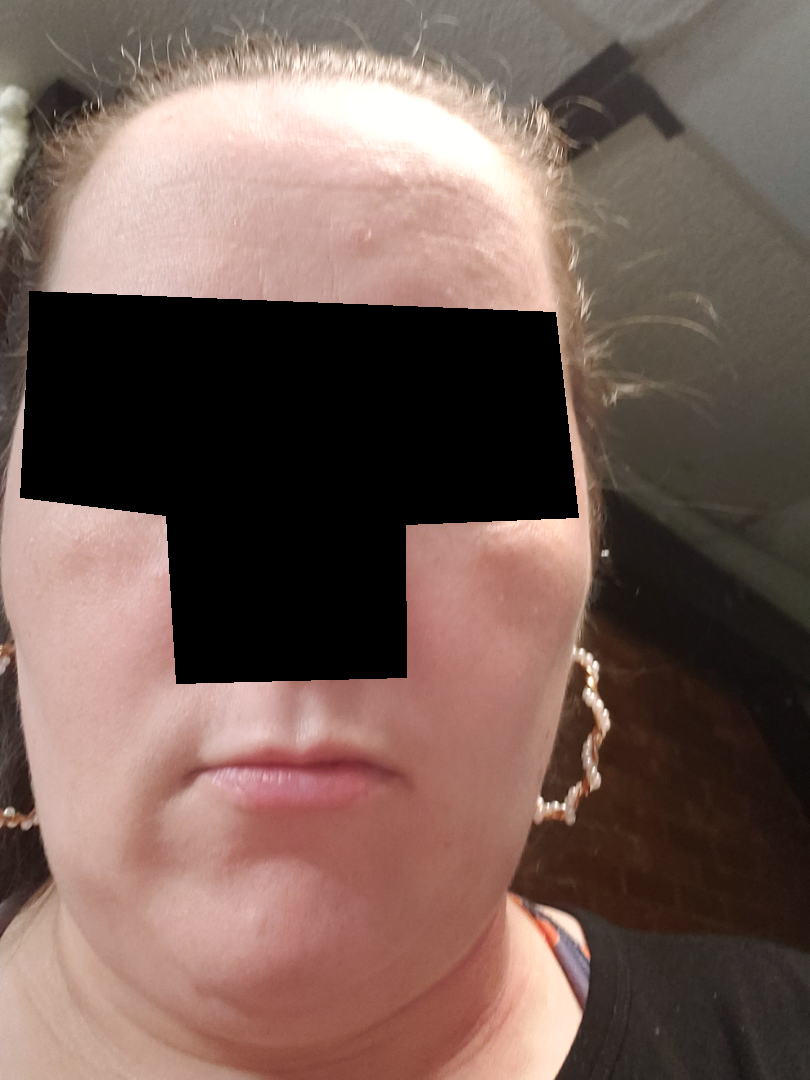Assessment: No discernible pathology was noted by the reviewing dermatologist. Clinical context: This is a close-up image. The subject is 30–39, female.